The lesion involves the arm. Female contributor, age 18–29. Present for less than one week. This image was taken at an angle. Texture is reported as raised or bumpy. The patient also reports fatigue.
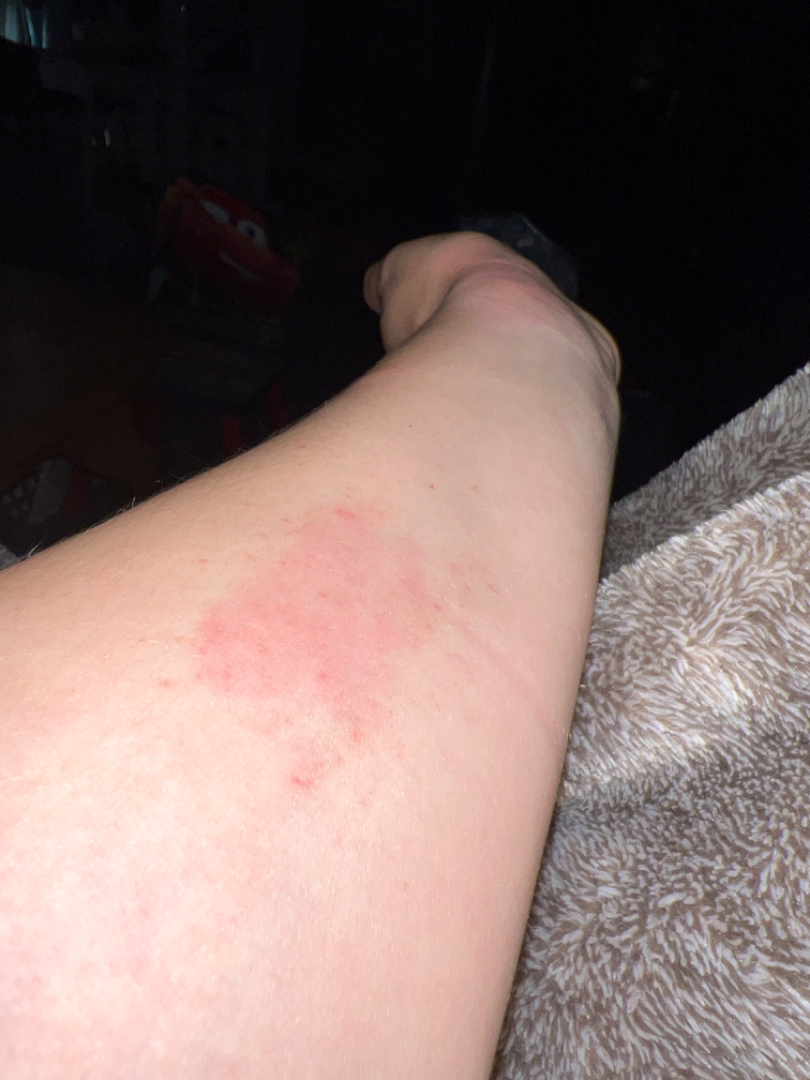On teledermatology review, the impression was split between Eczema, Hypersensitivity and Allergic Contact Dermatitis.